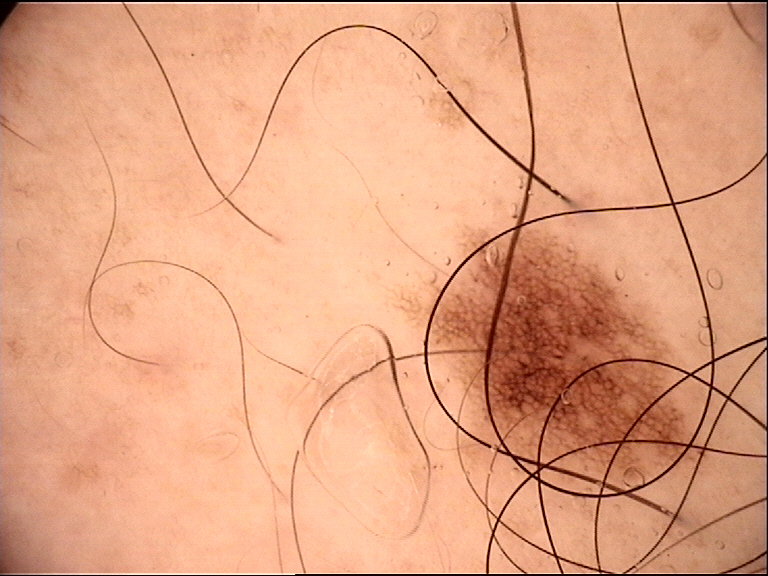The diagnostic label was a dysplastic junctional nevus.